A dermoscopic close-up of a skin lesion, the patient is a female about 50 years old: 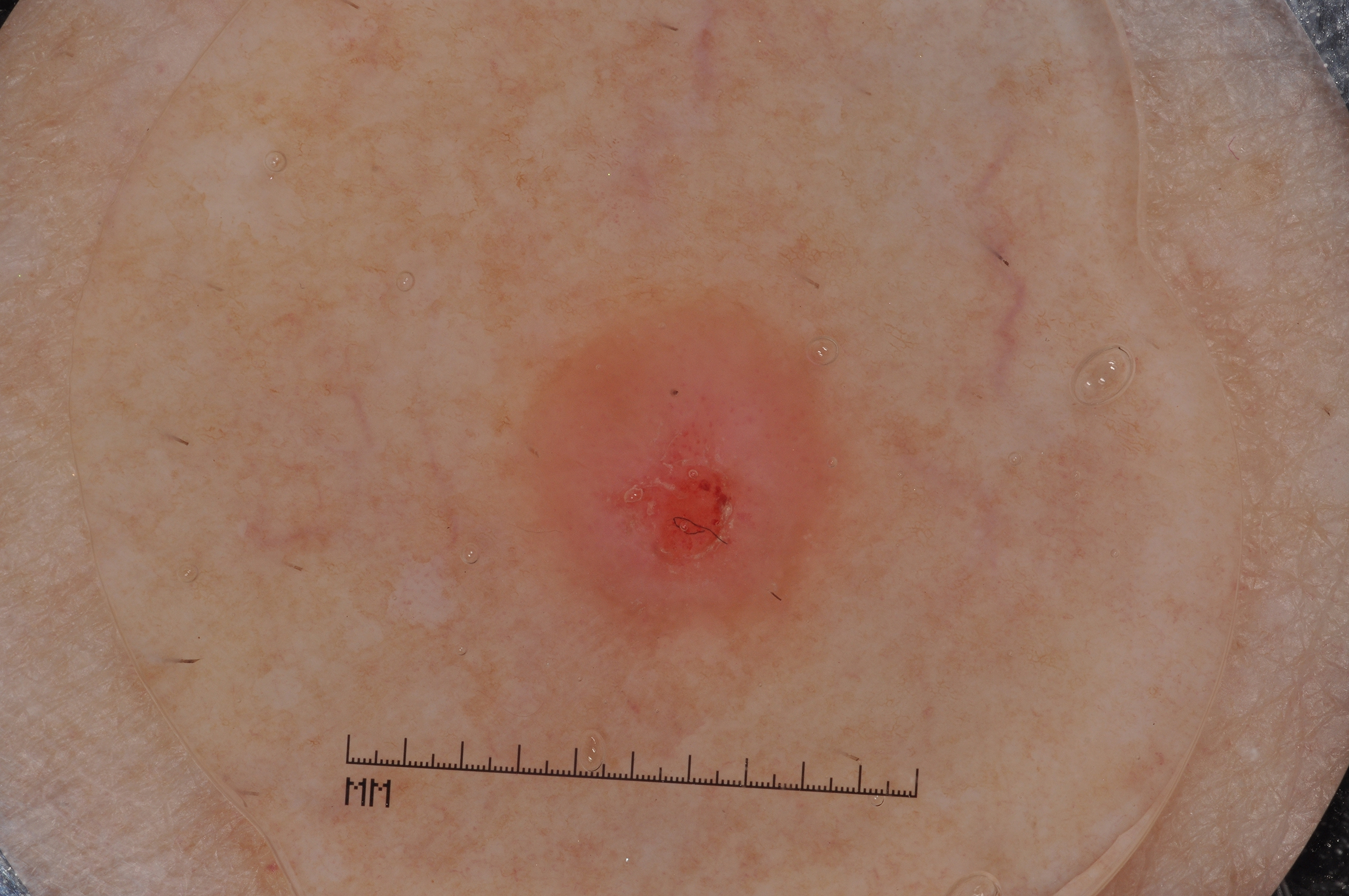{
  "lesion_location": {
    "bbox_xyxy": [
      495,
      287,
      885,
      665
    ]
  },
  "lesion_extent": "moderate",
  "dermoscopic_features": {
    "present": [],
    "absent": [
      "streaks",
      "milia-like cysts",
      "negative network",
      "pigment network"
    ]
  },
  "diagnosis": {
    "name": "melanoma",
    "malignancy": "malignant",
    "lineage": "melanocytic",
    "provenance": "histopathology"
  }
}